Located on the leg. Close-up view. Female subject, age 40–49 — 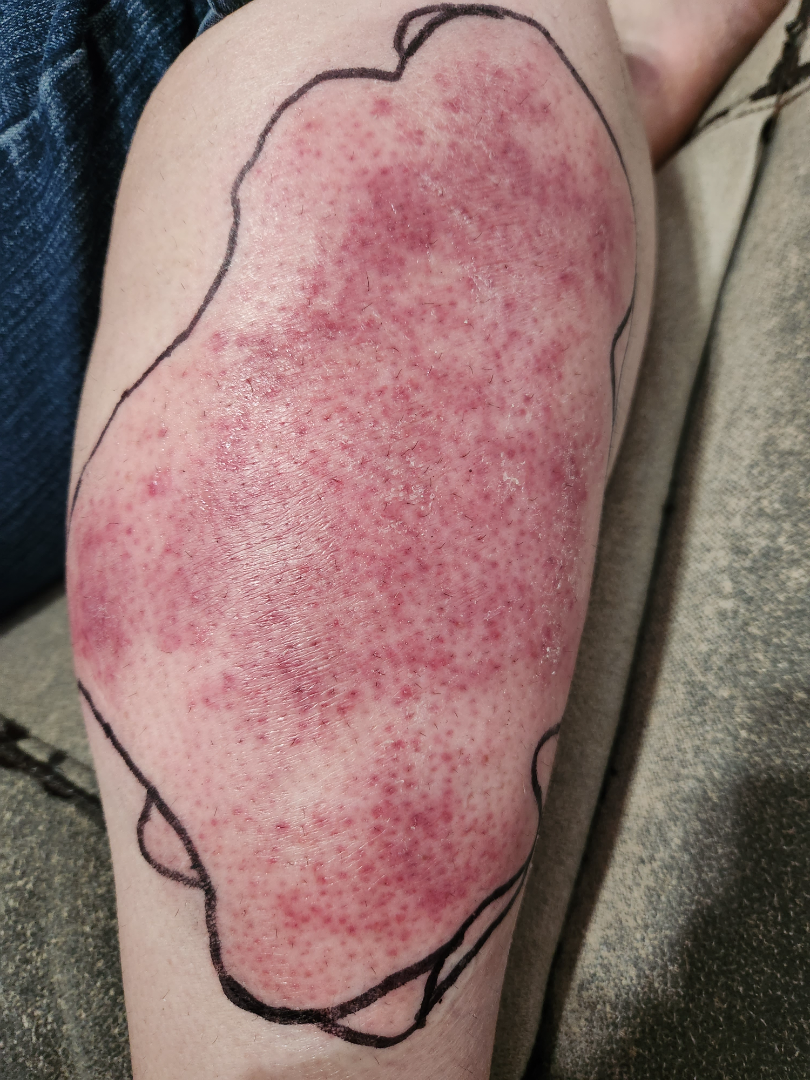Q: Reported symptoms?
A: darkening, bothersome appearance, burning and pain
Q: Patient's own categorization?
A: a rash
Q: Duration?
A: less than one week
Q: Any systemic symptoms?
A: fatigue and chills
Q: What is the lesion texture?
A: raised or bumpy
Q: What is the differential diagnosis?
A: favoring Cellulitis; possibly Localized cutaneous vasculitis